A dermatoscopic image of a skin lesion: 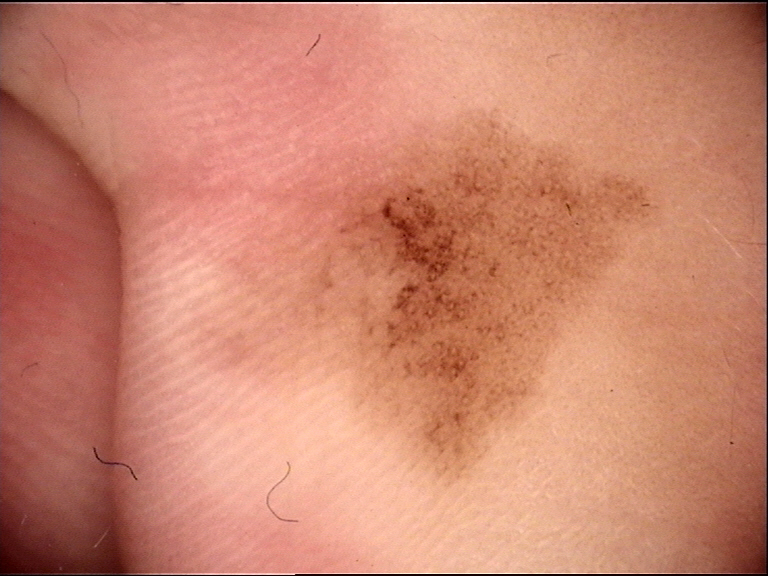Diagnosed as a banal lesion — an acral junctional nevus.